A dermoscopic image of a skin lesion:
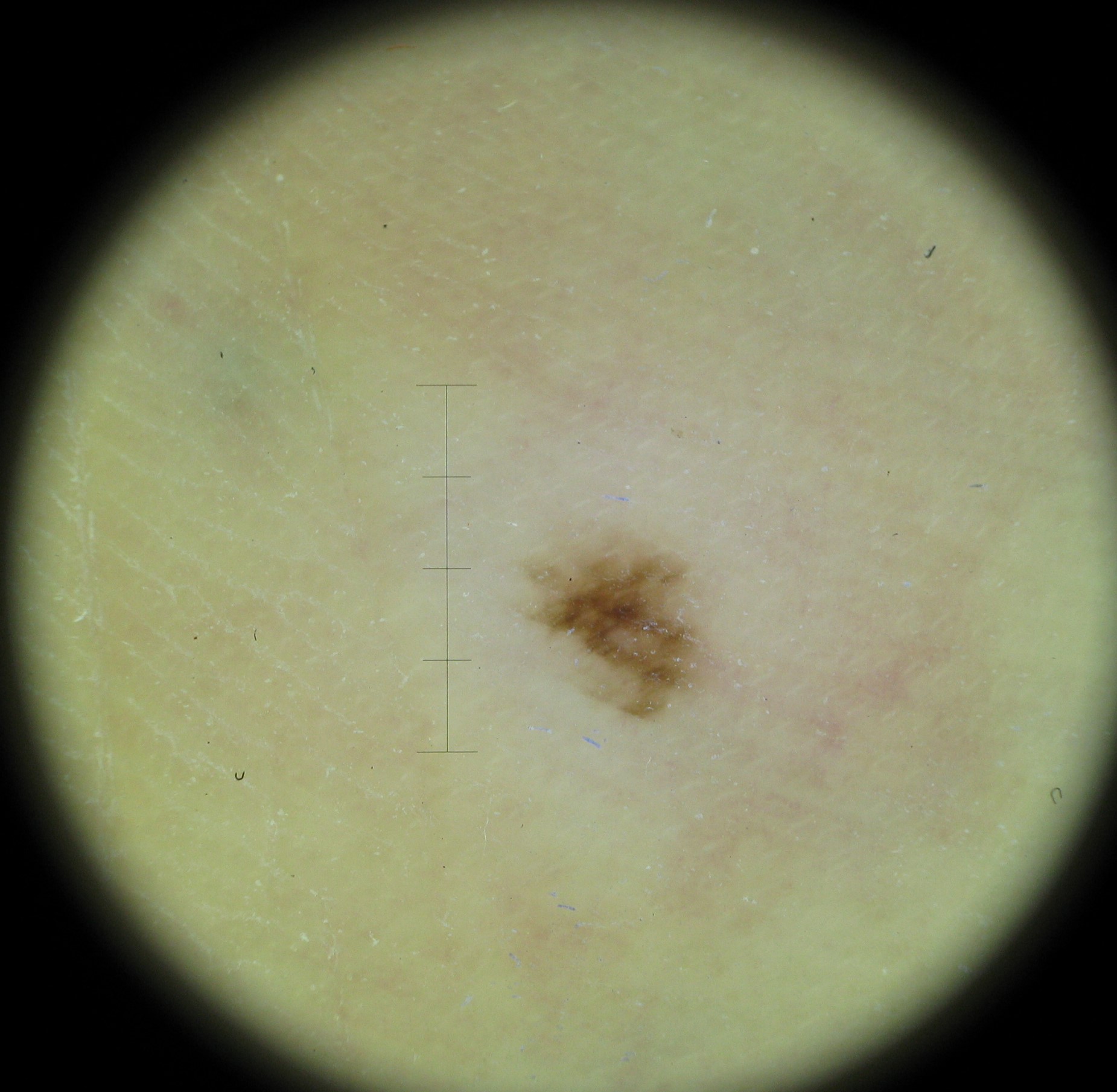<dermoscopy>
  <diagnosis>
    <name>acral dysplastic junctional nevus</name>
    <code>ajd</code>
    <malignancy>benign</malignancy>
    <super_class>melanocytic</super_class>
    <confirmation>expert consensus</confirmation>
  </diagnosis>
</dermoscopy>